This is a close-up image.
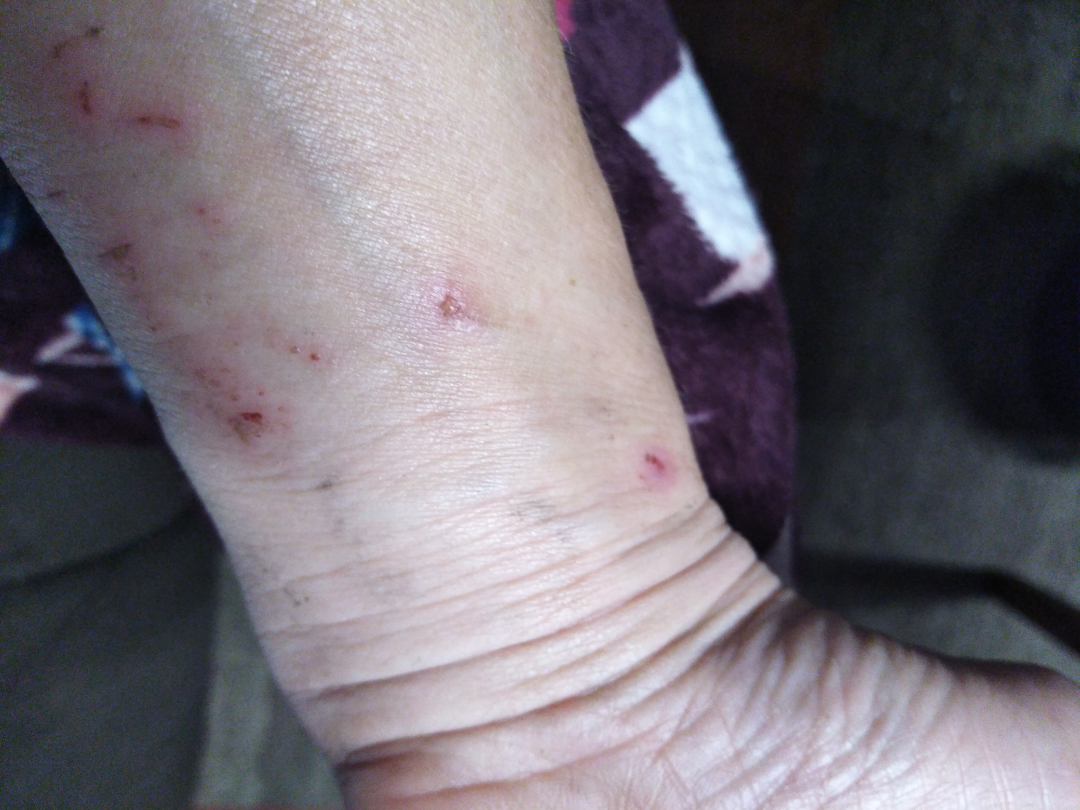Findings:
– assessment: not assessable
– skin tone: Fitzpatrick skin type IV